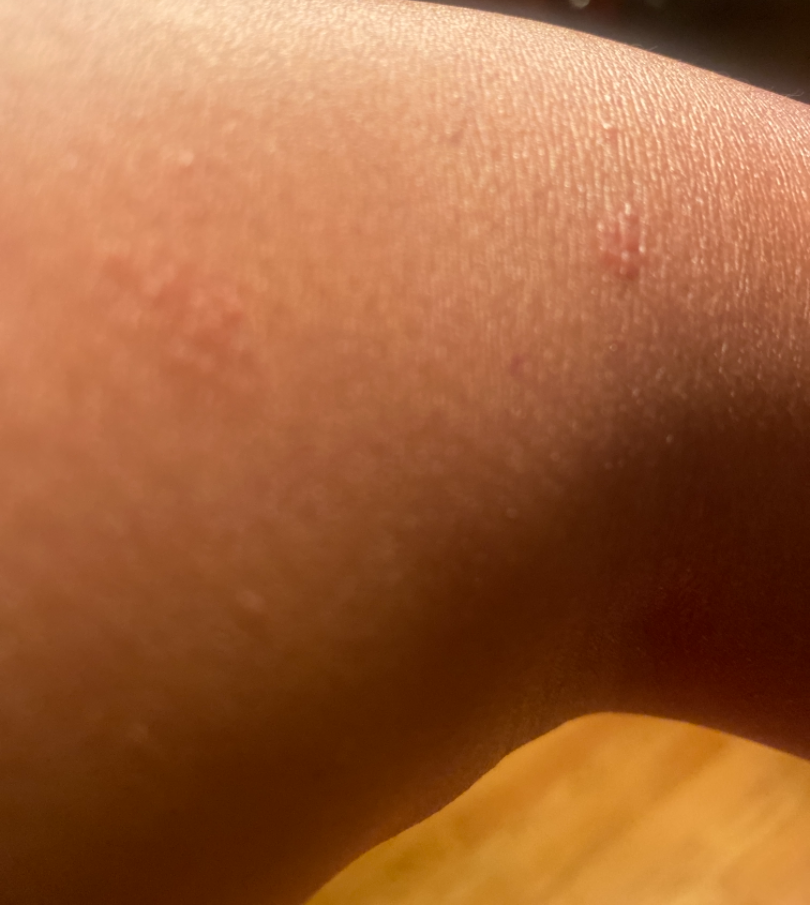Review:
The reviewer was unable to grade this case for skin condition.